A dermoscopic close-up of a skin lesion:
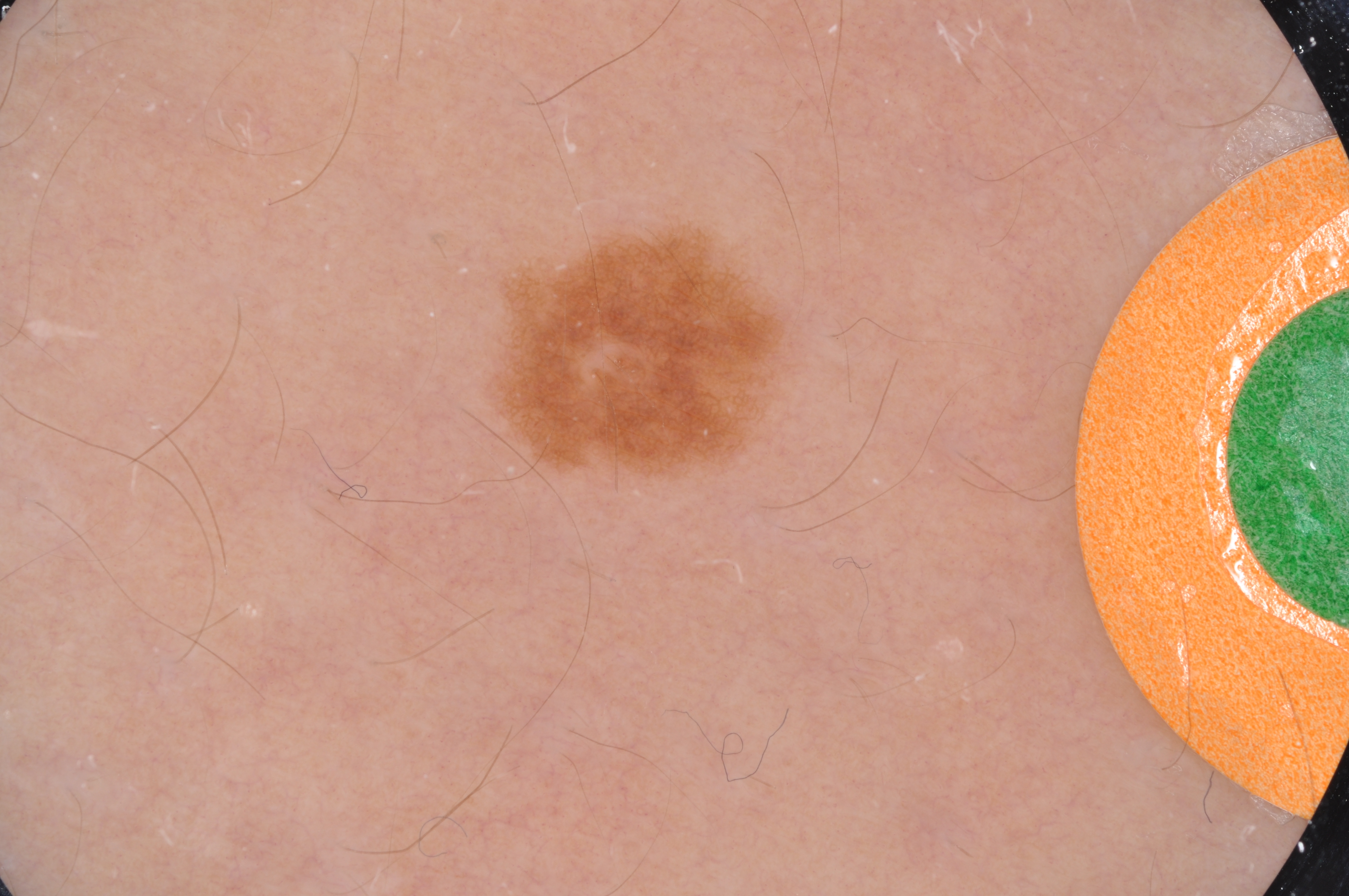dermoscopic_features:
  present:
    - pigment network
  absent:
    - globules
    - streaks
    - negative network
    - milia-like cysts
lesion_location:
  bbox_xyxy:
    - 469
    - 203
    - 800
    - 484
diagnosis:
  name: melanocytic nevus
  malignancy: benign
  lineage: melanocytic
  provenance: clinical